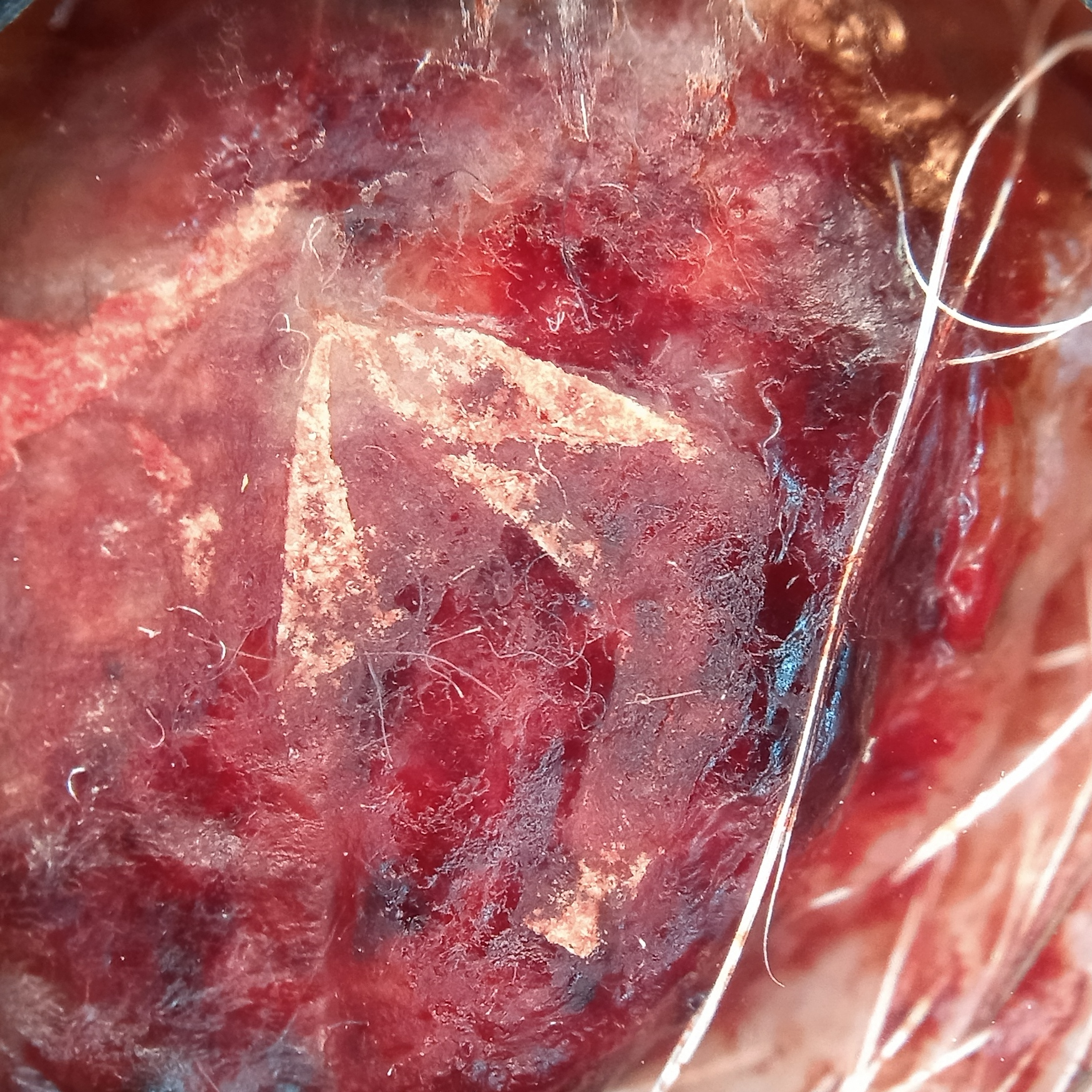The patient says their skin reddens with sun exposure.
Referred for assessment of suspected melanoma.
The patient reports a personal history of cancer.
A male patient 78 years of age.
Few moles overall by the patient's own estimate.
Confirmed on histopathology as a melanoma, following excision.